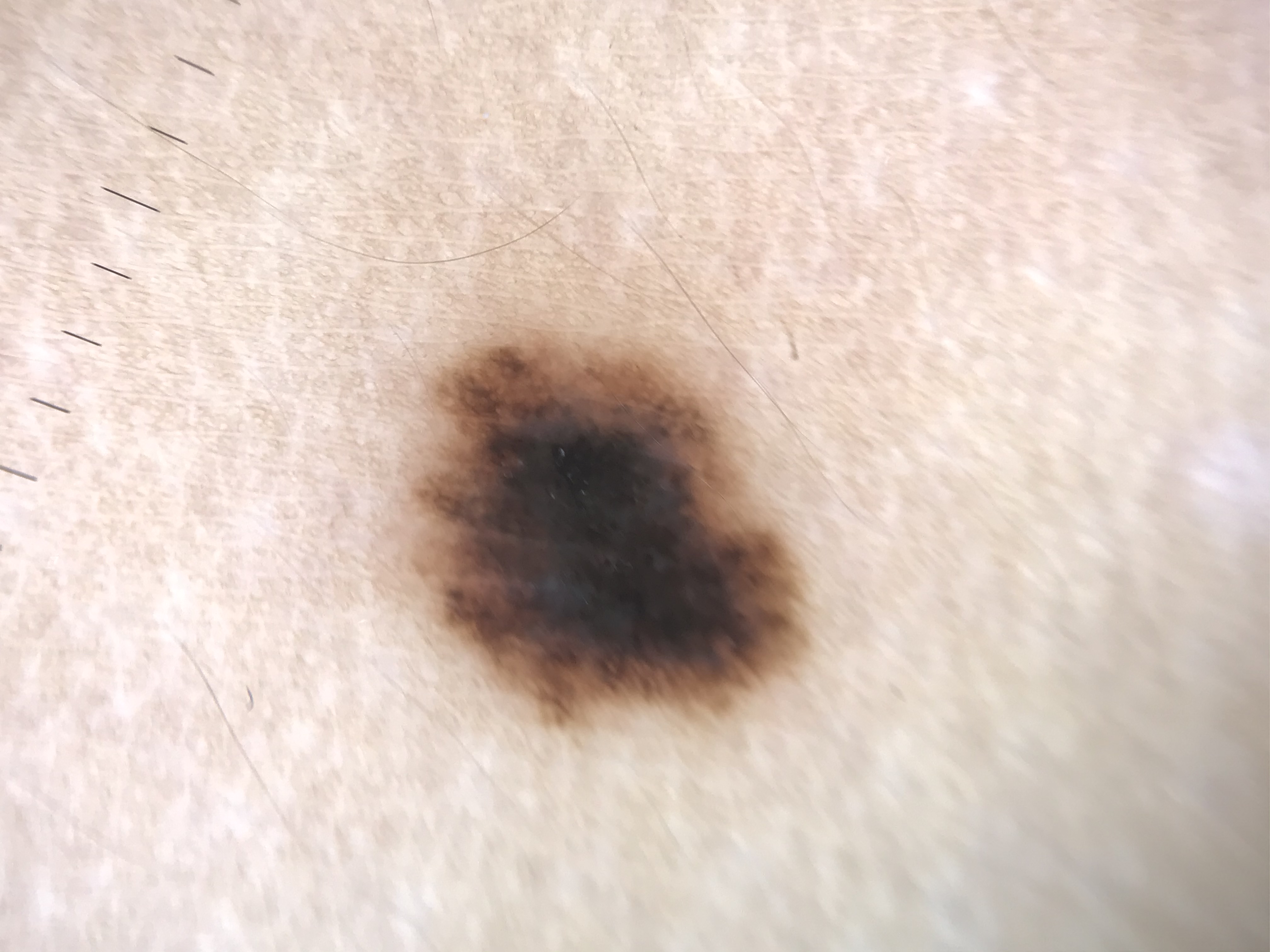Dermoscopy of a skin lesion.
Diagnosed as a dysplastic junctional nevus.